Associated systemic symptoms include chills. The lesion is described as raised or bumpy. The patient is a female aged 60–69. A close-up photograph. No associated lesion symptoms were reported. Located on the leg. The condition has been present for less than one week. The patient described the issue as acne: 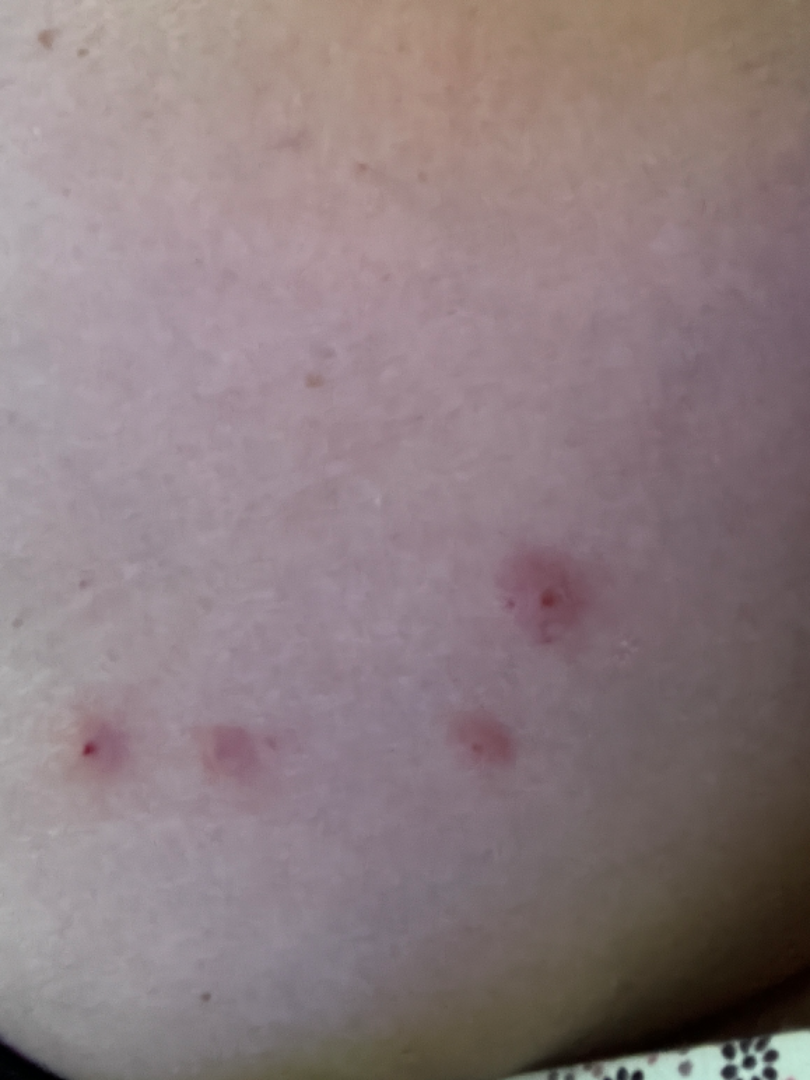On remote review of the image, the reviewer's impression was Insect Bite.